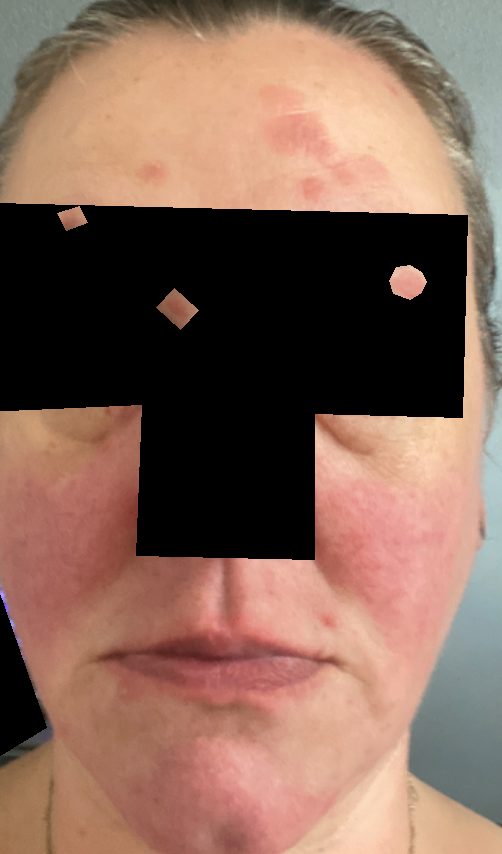Close-up view. The patient considered this a rash. The lesion is associated with burning, bothersome appearance and itching. Female contributor, age 40–49. The contributor notes the lesion is rough or flaky, flat and raised or bumpy. The affected area is the head or neck. A single dermatologist reviewed the case: Rosacea, Allergic Contact Dermatitis and Systemic lupus erythematosus-related syndrome were considered with similar weight.